A dermatoscopic image of a skin lesion:
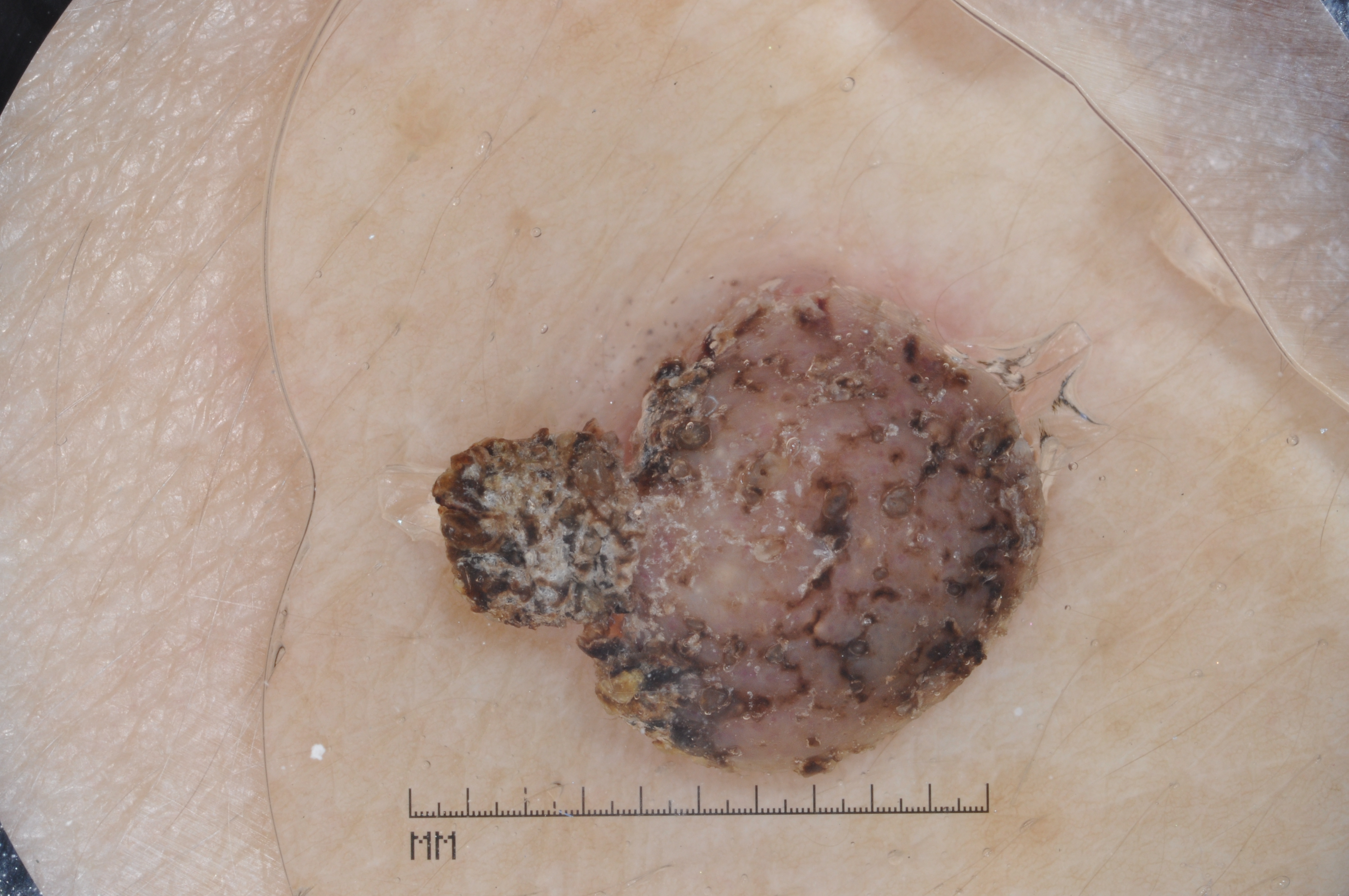<case>
  <dermoscopic_features>
    <present>milia-like cysts</present>
    <absent>negative network, streaks, pigment network</absent>
  </dermoscopic_features>
  <lesion_location>
    <bbox_xyxy>443, 273, 1054, 784</bbox_xyxy>
  </lesion_location>
  <diagnosis>
    <name>seborrheic keratosis</name>
    <malignancy>benign</malignancy>
    <lineage>keratinocytic</lineage>
    <provenance>clinical</provenance>
  </diagnosis>
</case>